Fitzpatrick phototype IV; lay reviewers estimated MST 4–5 · a close-up photograph:
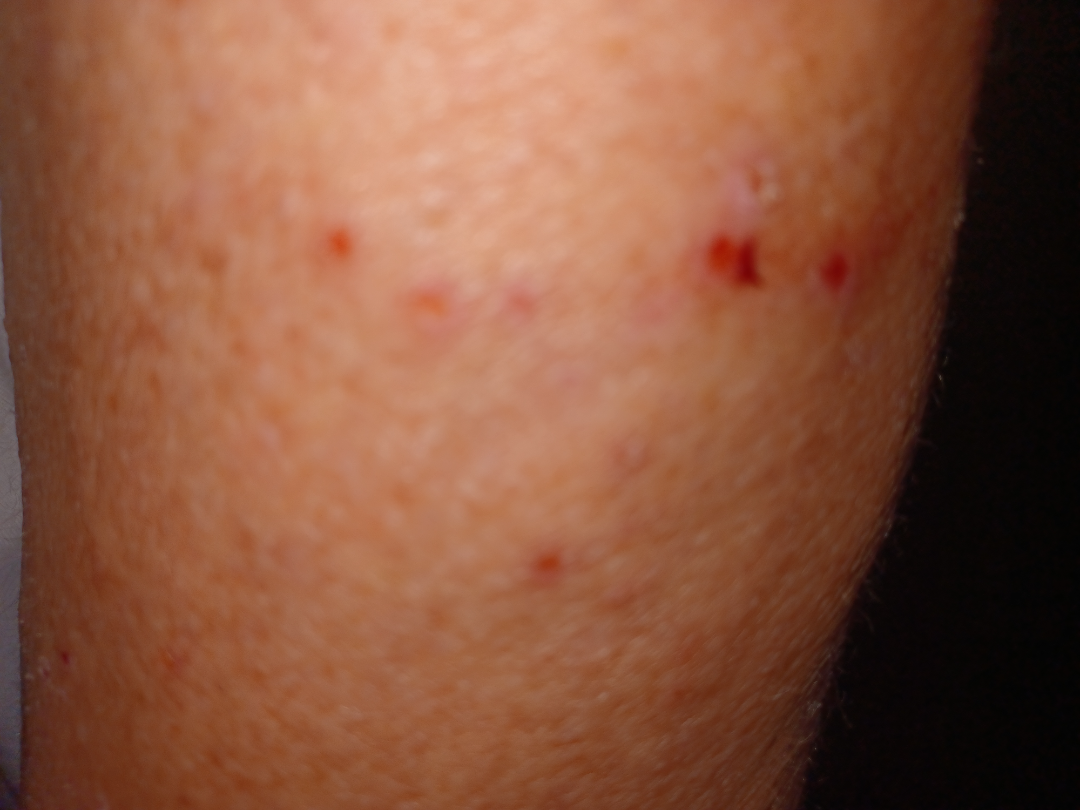Case summary:
- assessment: could not be assessed